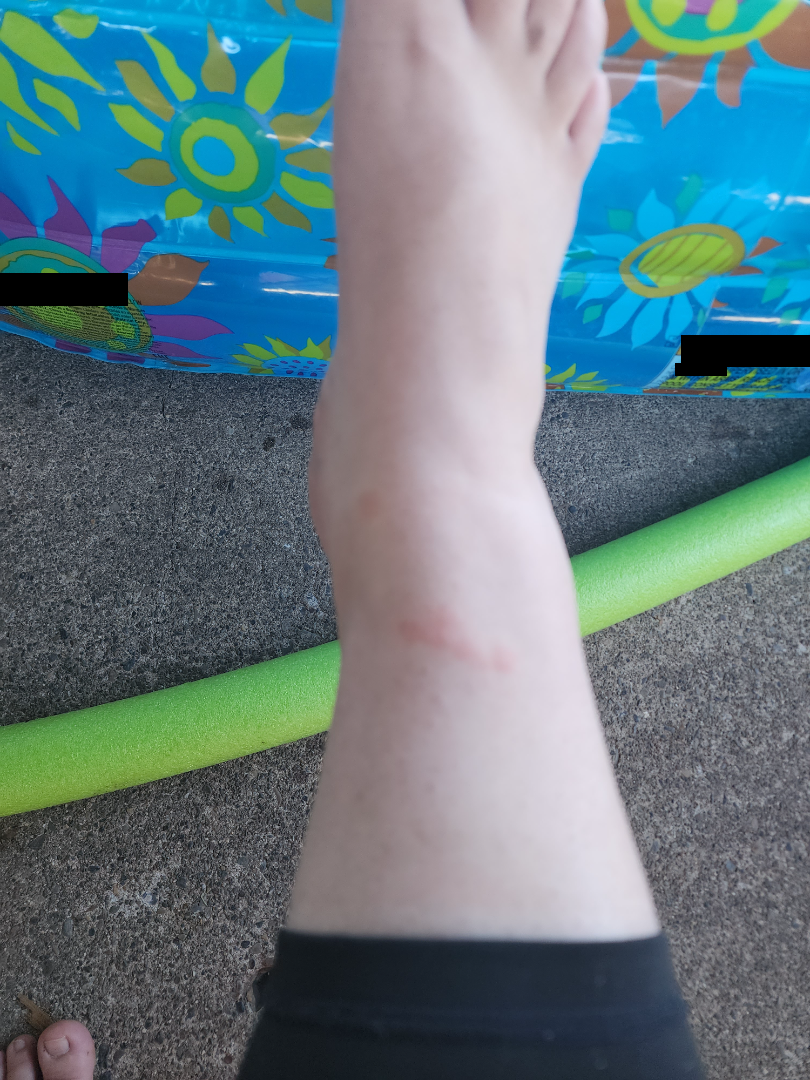{
  "assessment": "indeterminate"
}